The lesion involves the back of the hand, reported lesion symptoms include itching, present for less than one week, the lesion is described as raised or bumpy, the photograph is a close-up of the affected area:
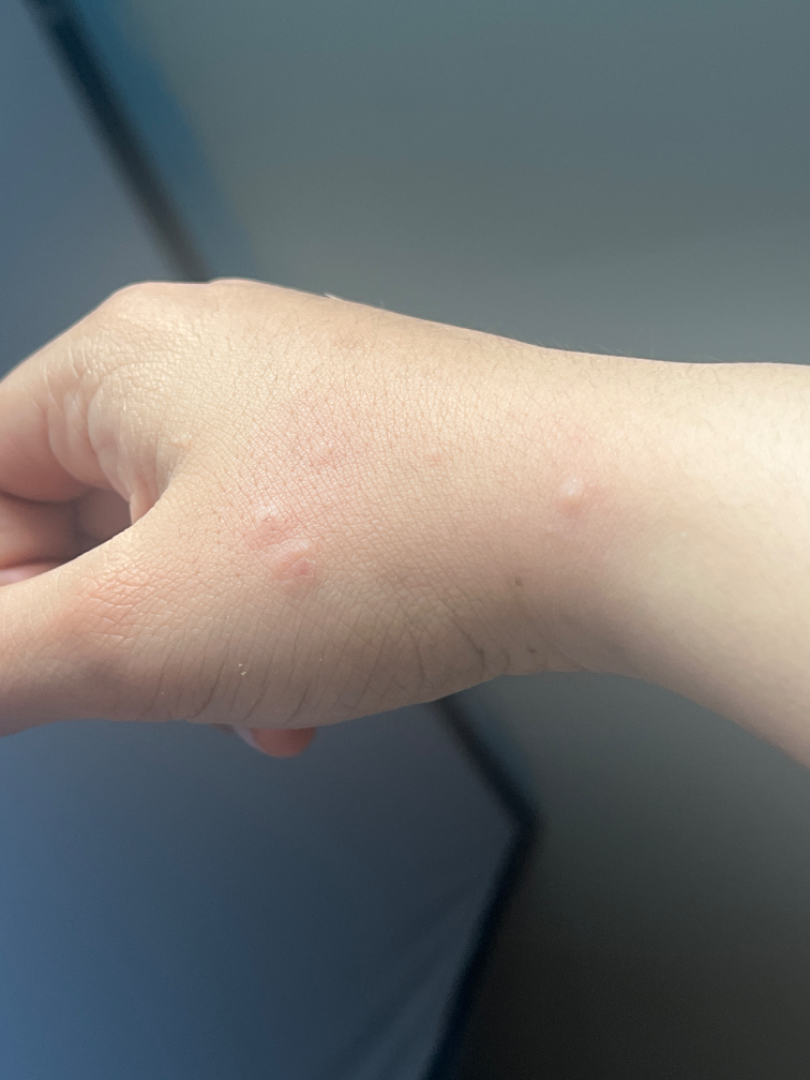Notes:
* differential — Urticaria and Insect Bite were each considered, in no particular order